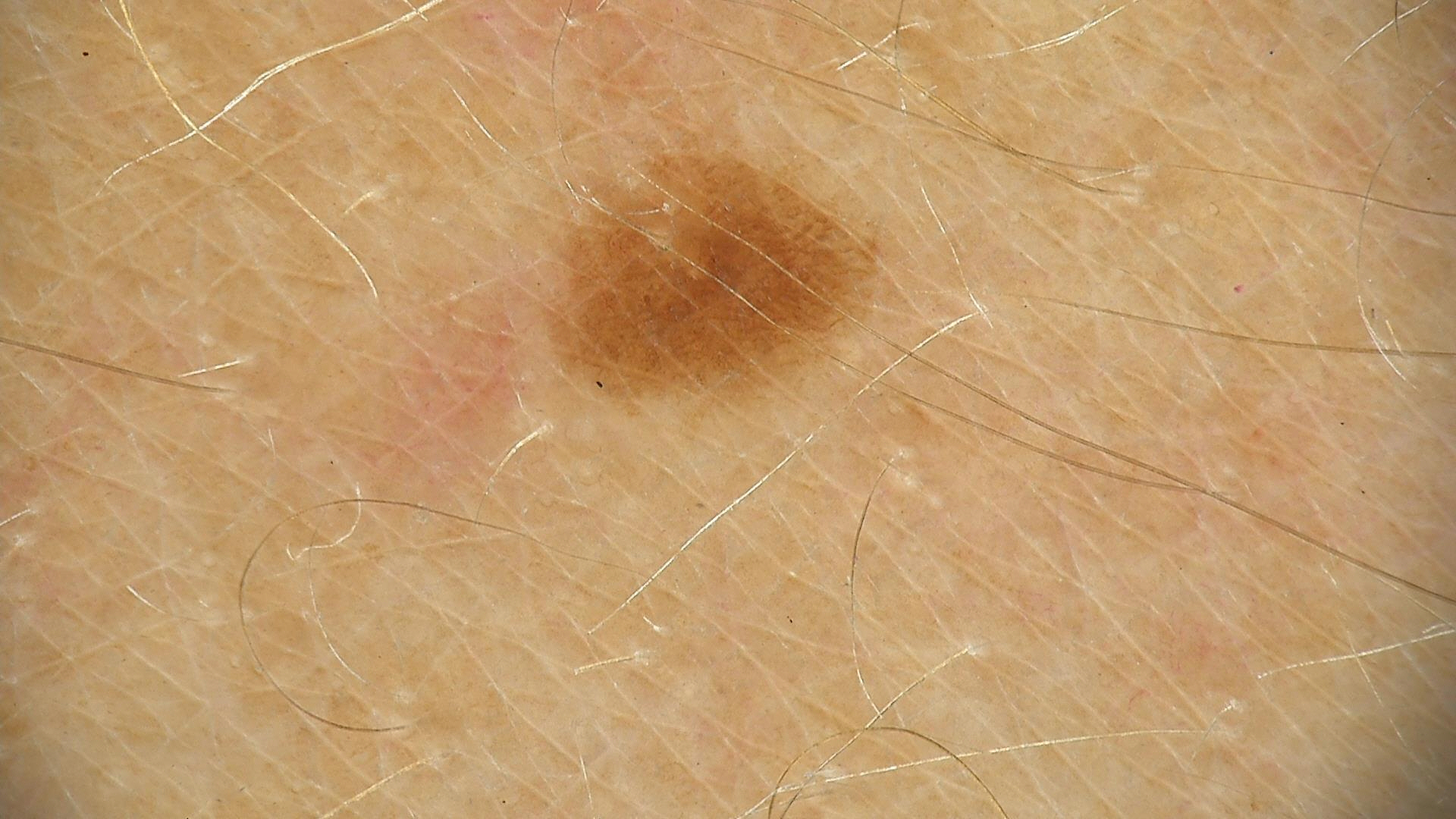Case:
The morphology is that of a banal lesion.
Impression:
The diagnosis was a junctional nevus.